A dermoscopy image of a single skin lesion.
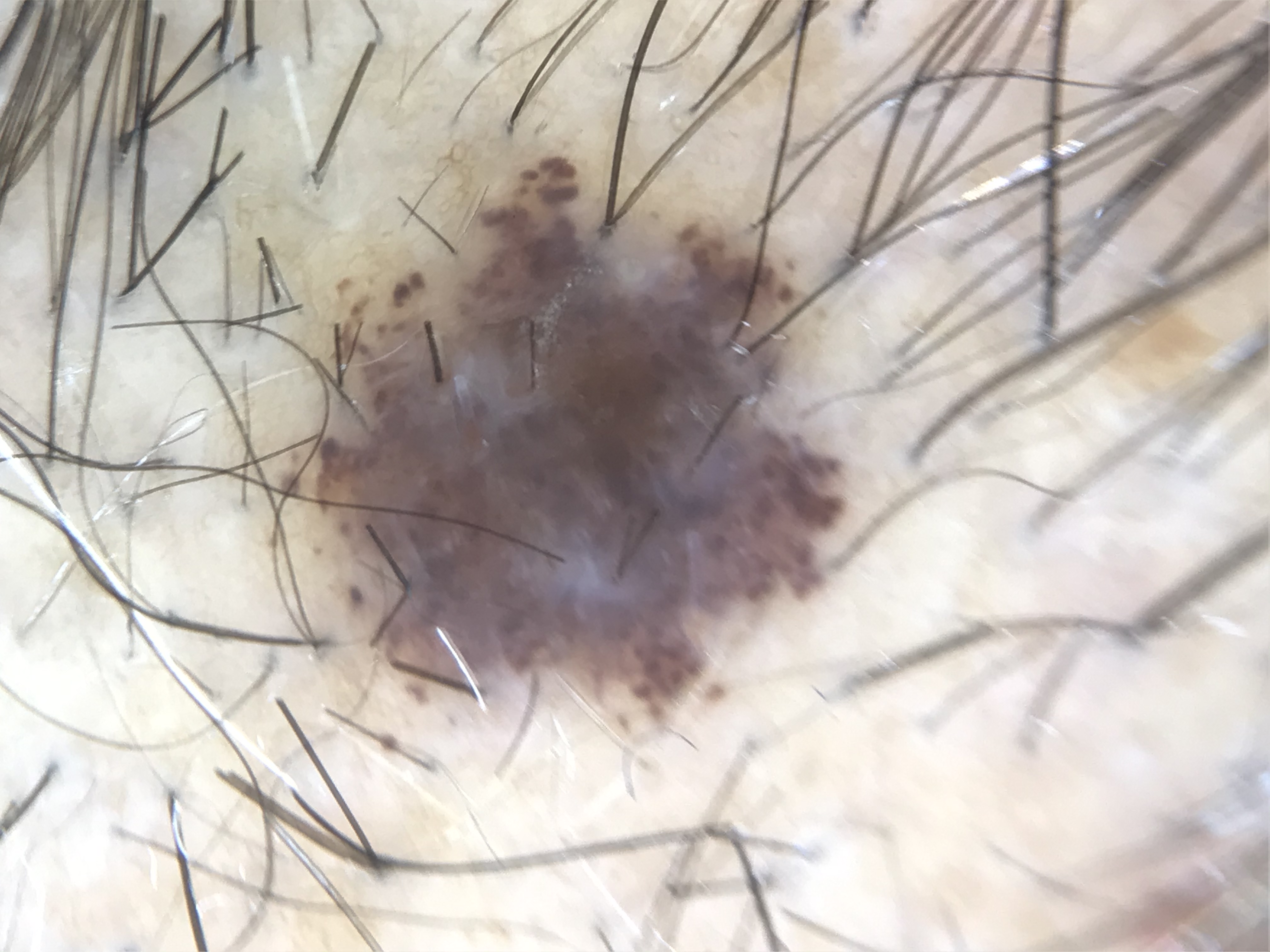Conclusion:
The diagnostic label was a benign lesion — a dysplastic compound nevus.